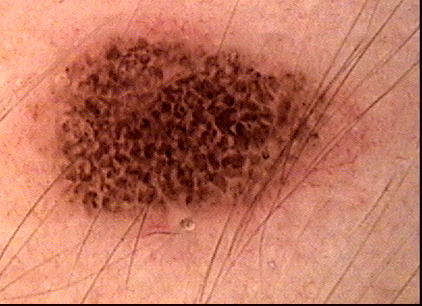Q: What is the imaging modality?
A: dermoscopy
Q: What is the lesion category?
A: banal
Q: What was the diagnostic impression?
A: compound nevus (expert consensus)